A dermatoscopic image of a skin lesion.
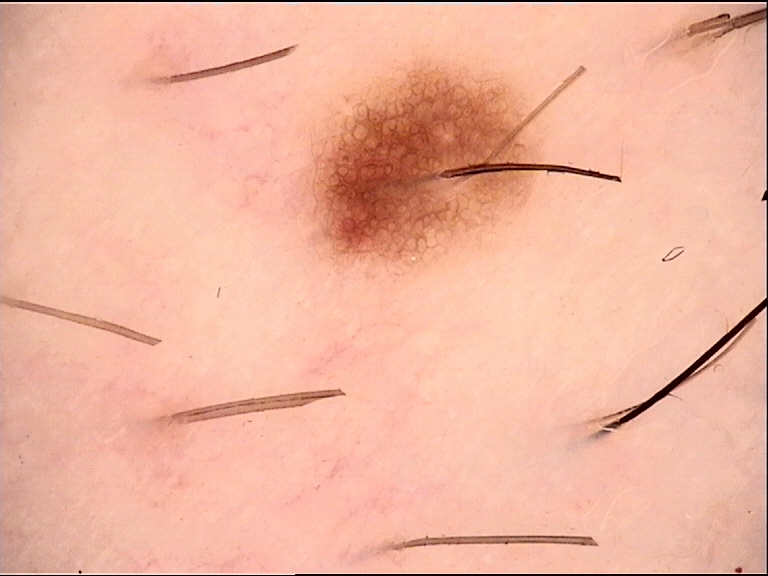• diagnosis — dysplastic junctional nevus (expert consensus)